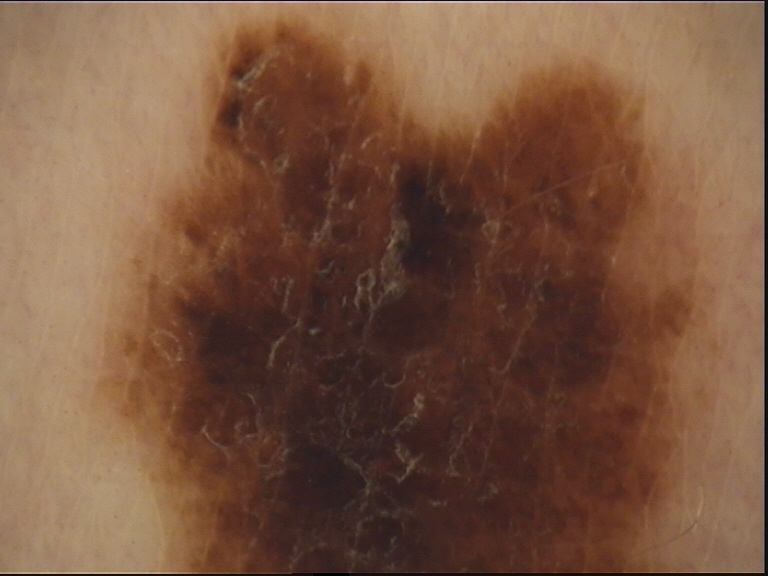Diagnosed as a dysplastic compound nevus.